Texture is reported as rough or flaky; the lesion involves the sole of the foot and palm; the condition has been present for three to twelve months; the photograph is a close-up of the affected area; female subject, age 18–29: 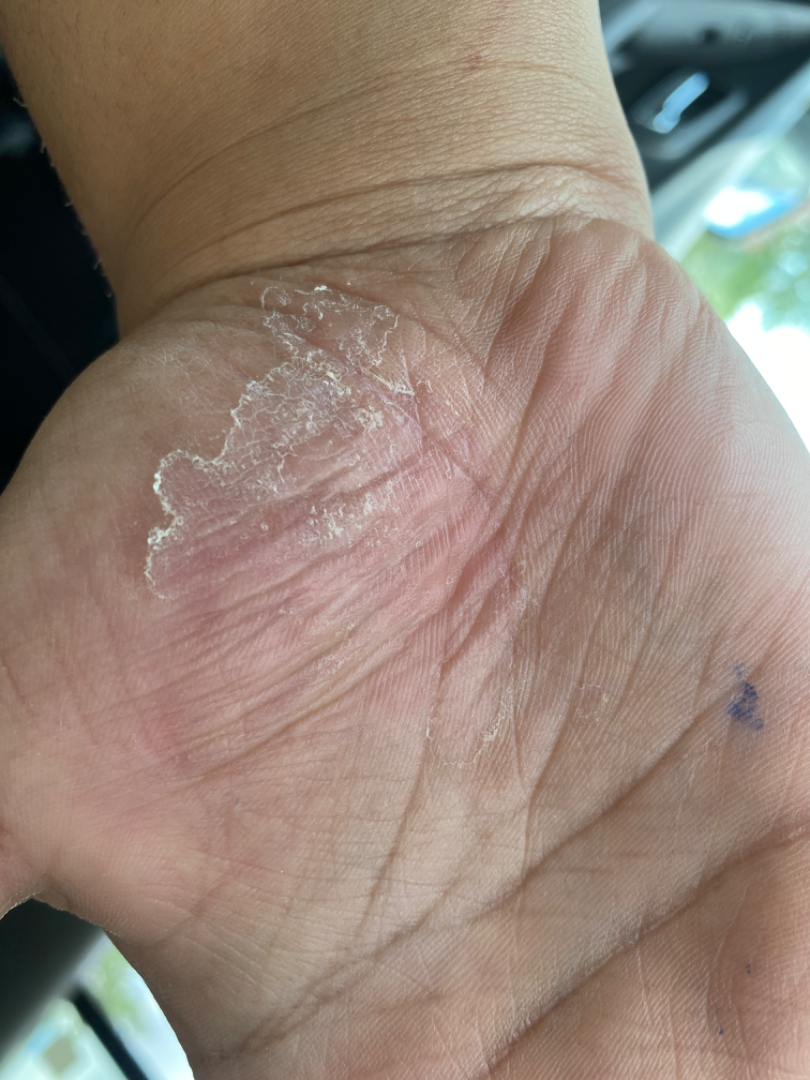Q: What conditions are considered?
A: three independent reviewers: most likely Psoriasis; also on the differential is Tinea; also raised was Irritant Contact Dermatitis; a remote consideration is Eczema; less probable is Allergic Contact Dermatitis